This is a close-up image. The lesion is described as raised or bumpy. Reported duration is one to four weeks. No relevant systemic symptoms. The contributor notes itching and burning. The affected area is the head or neck. Female subject, age 30–39. The patient described the issue as a rash.
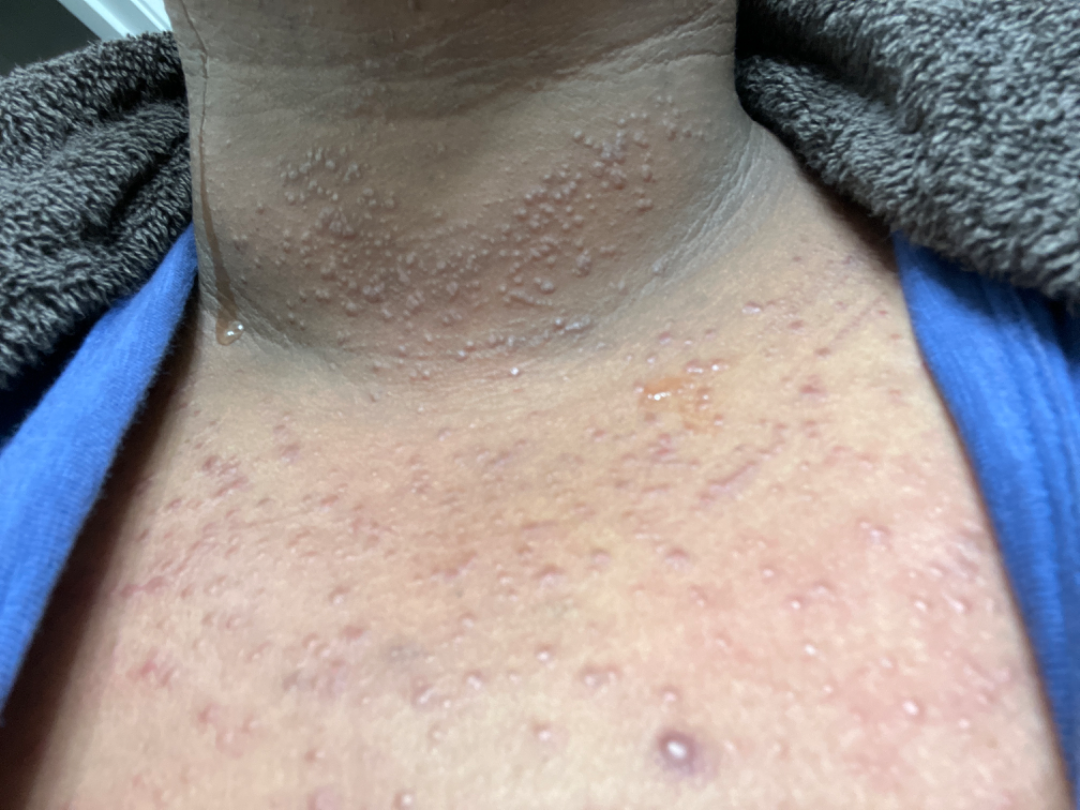On photographic review: most likely Adnexal neoplasm; also consider Folliculitis; the differential also includes Miliaria; less probable is Cyst; less likely is Lichen planus/lichenoid eruption.